Located on the head or neck · the photo was captured at an angle.
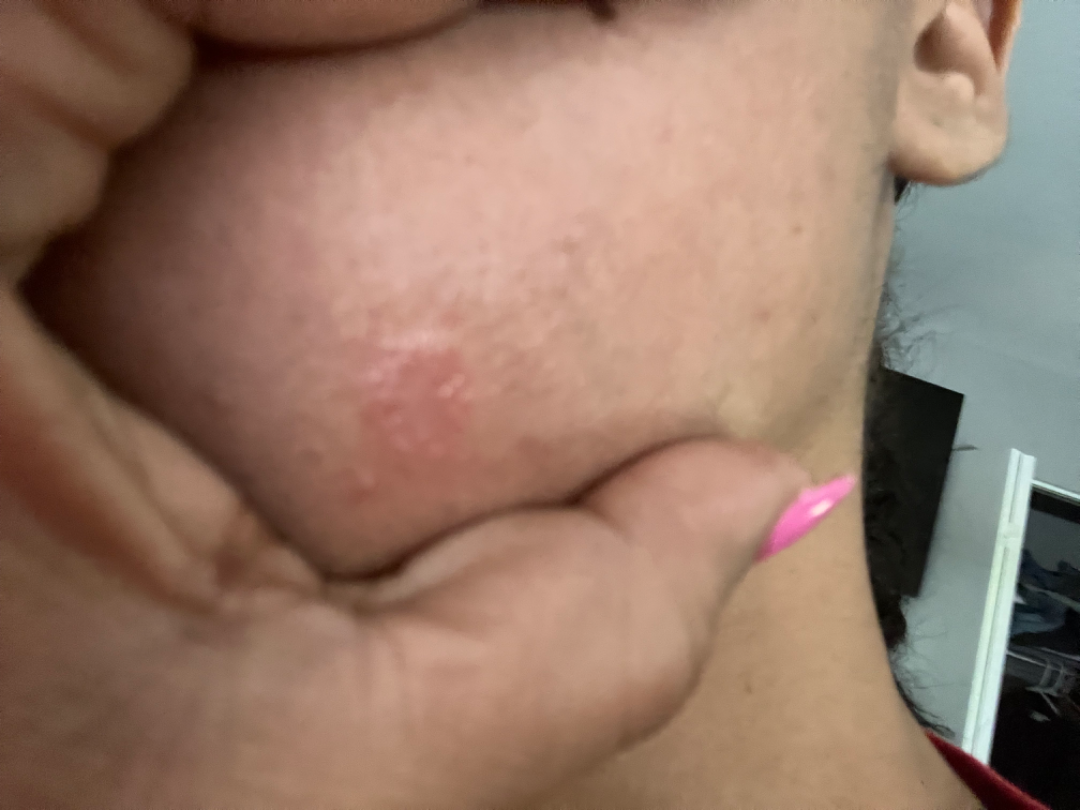Impression:
On dermatologist assessment of the image: most consistent with Tinea; also consider Impetigo; possibly Herpes Simplex.